Dermoscopy of a skin lesion — 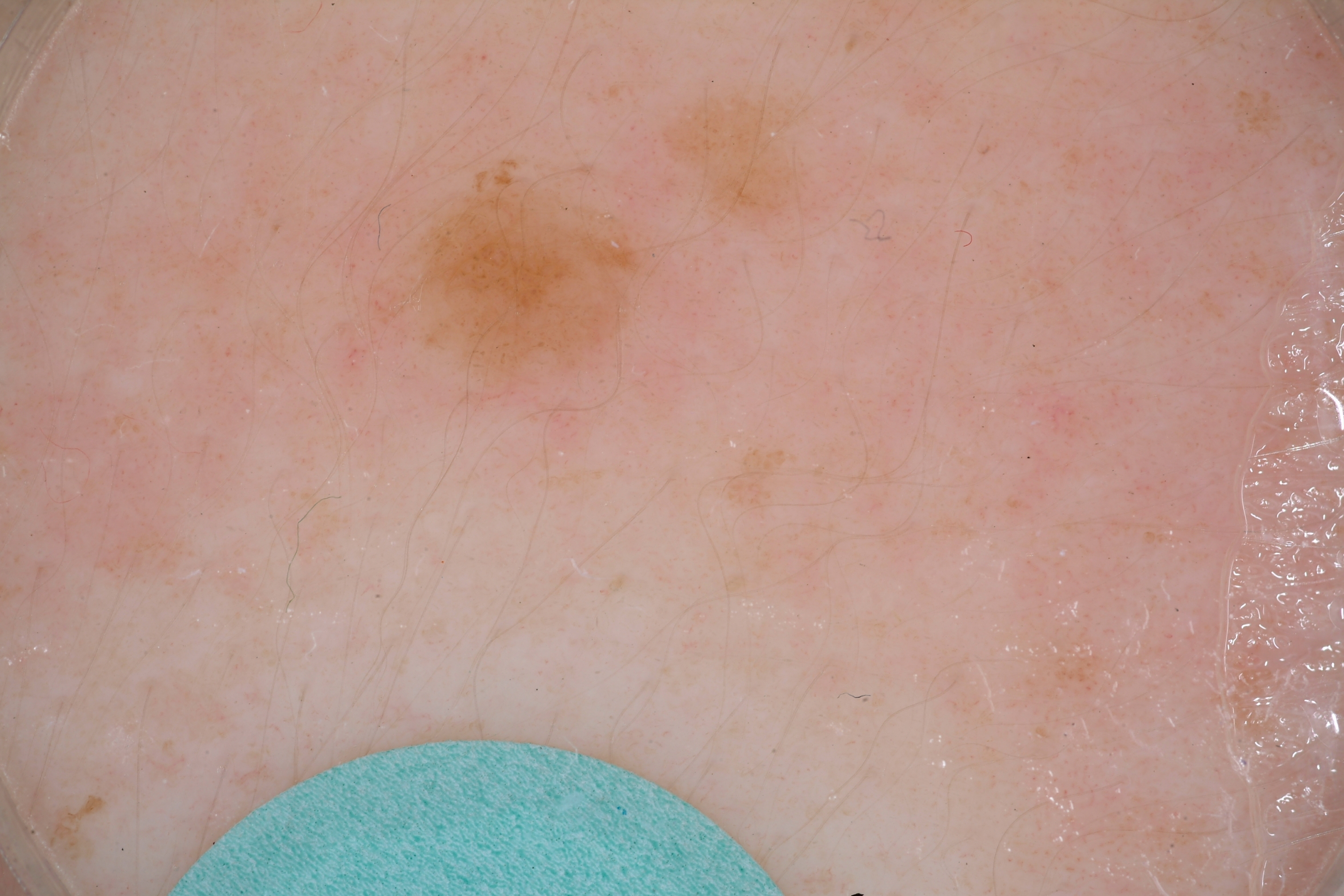{"lesion_location": {"bbox_xyxy": [404, 179, 647, 397]}, "dermoscopic_features": {"present": ["globules"], "absent": ["streaks"]}, "lesion_extent": "small", "diagnosis": {"malignancy": "benign", "provenance": "clinical"}}